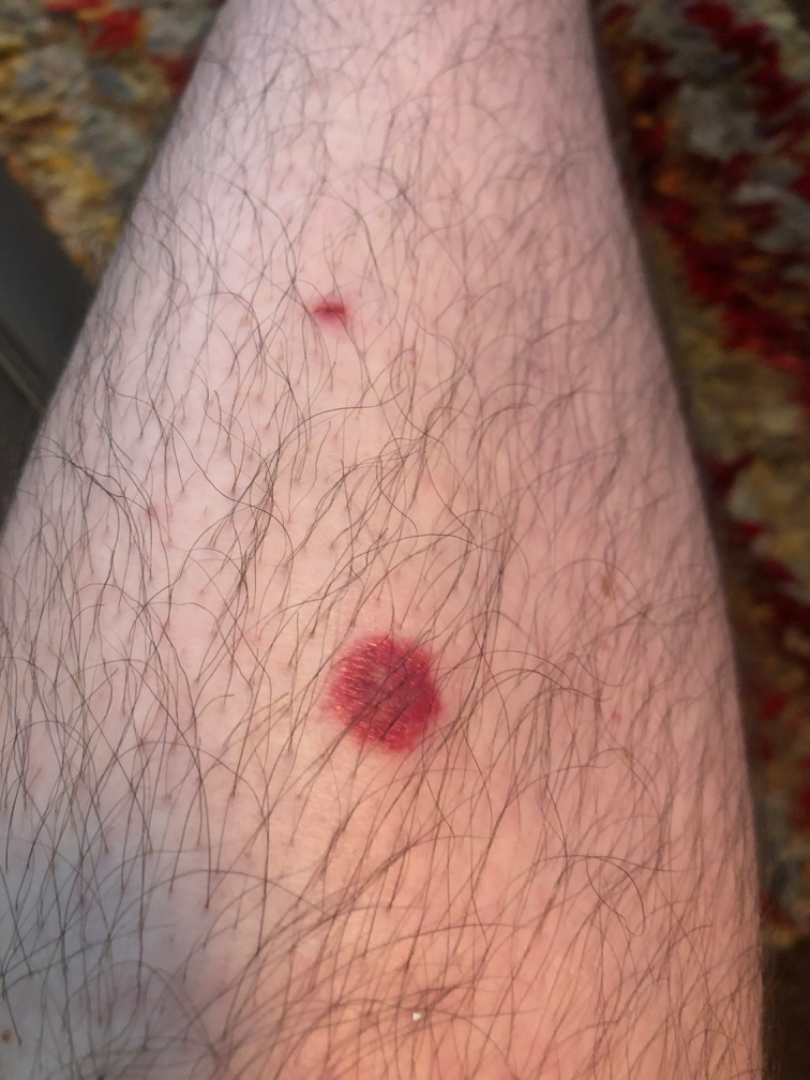Case summary:
* contributor · male, age 50–59
* shot type · at an angle
* site · leg
* texture · flat
* duration · about one day
* reported symptoms · bothersome appearance
* dermatologist impression · the differential, in no particular order, includes Insect Bite, Cutaneous sarcoidosis and Leukocytoclastic Vasculitis